The patient is a female aged approximately 25, a dermatoscopic image of a skin lesion.
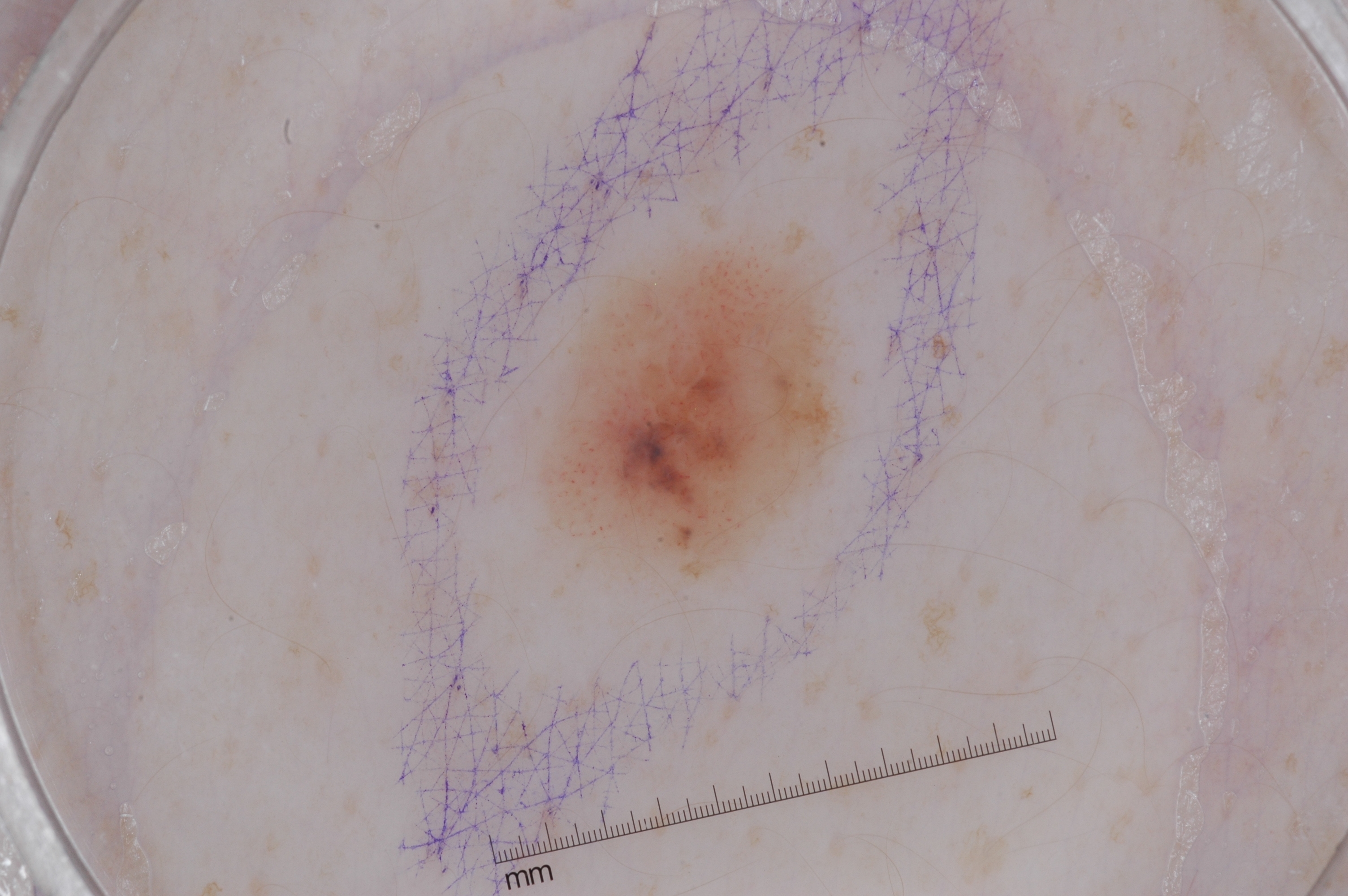Notes:
- location · [537,238,832,581]
- features · milia-like cysts and negative network; absent: streaks and pigment network
- diagnosis · a melanocytic nevus